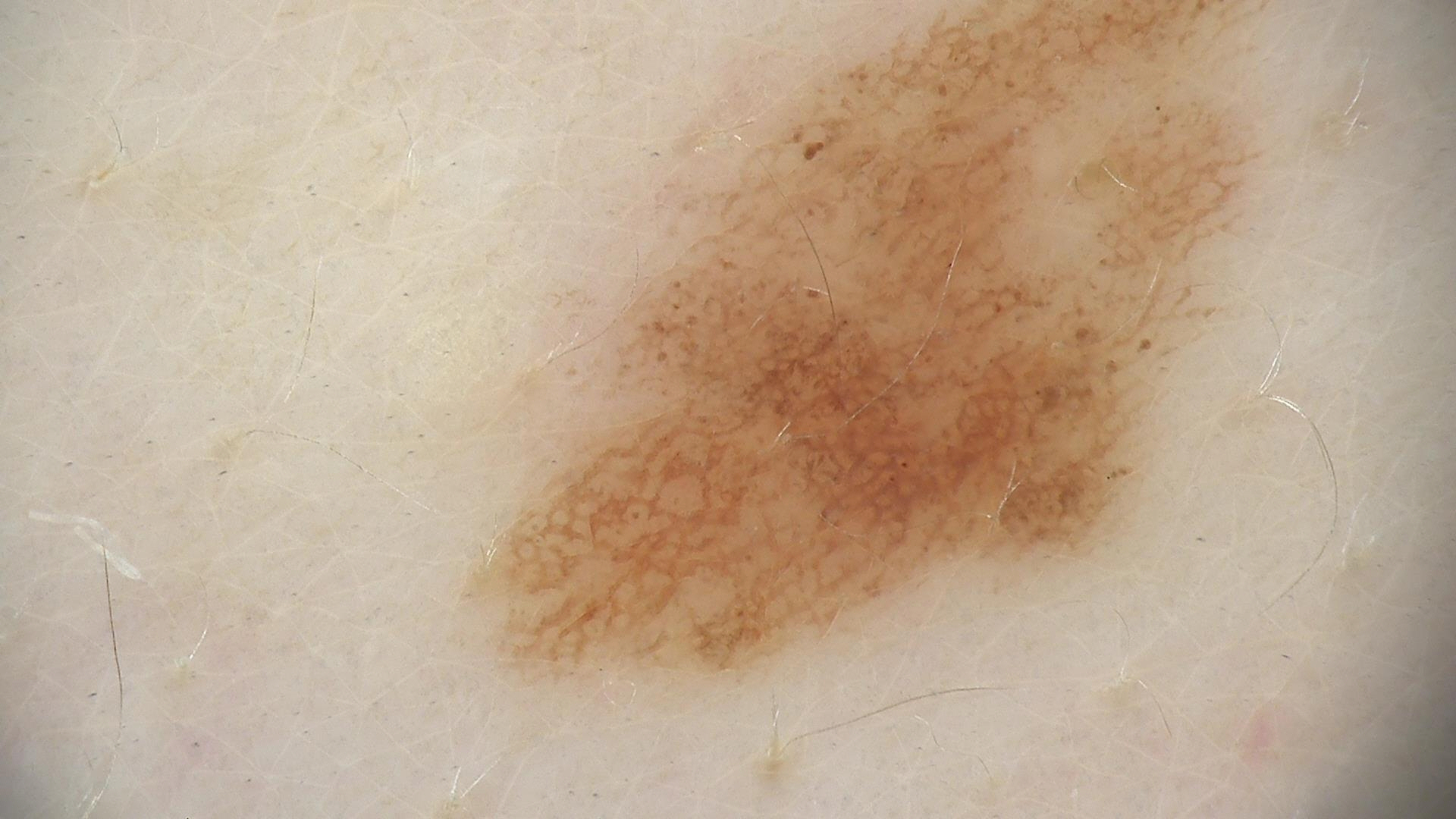Summary: A dermoscopic image of a skin lesion. Impression: The diagnostic label was a benign lesion — a dysplastic junctional nevus.